Close-up view · the affected area is the leg:
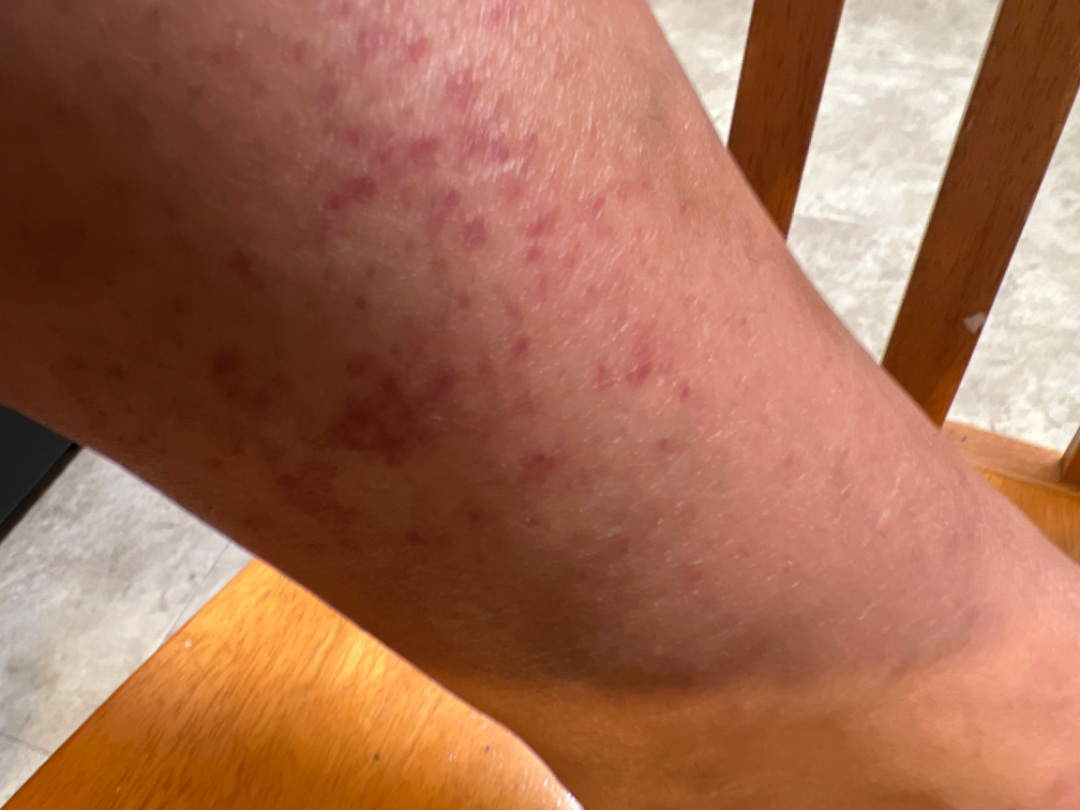Review:
The case was indeterminate on photographic review.
Patient information:
Reported lesion symptoms include bothersome appearance and enlargement. Skin tone: non-clinician graders estimated MST 2 or 5. The lesion is described as flat.